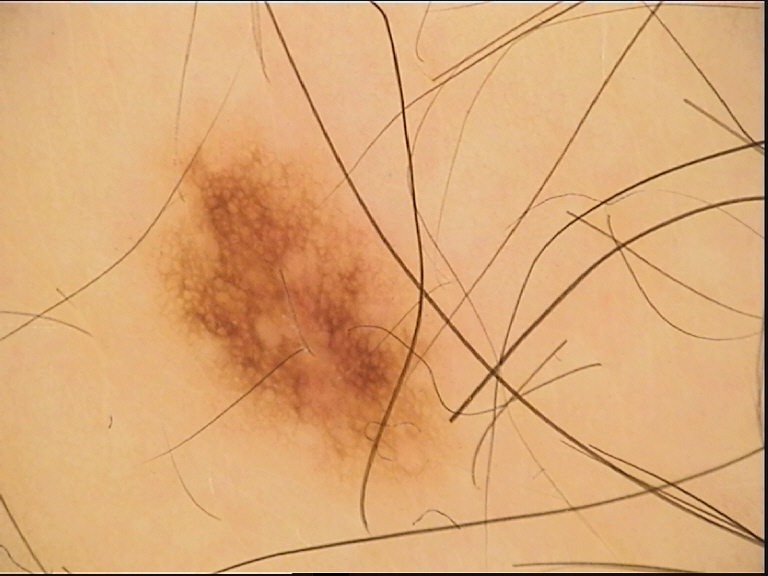Diagnosed as a dysplastic junctional nevus.